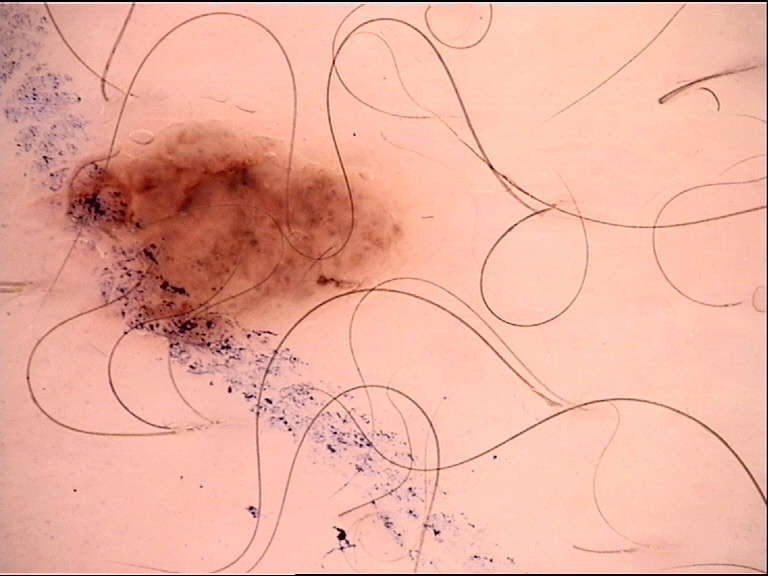Conclusion:
Diagnosed as a compound nevus.